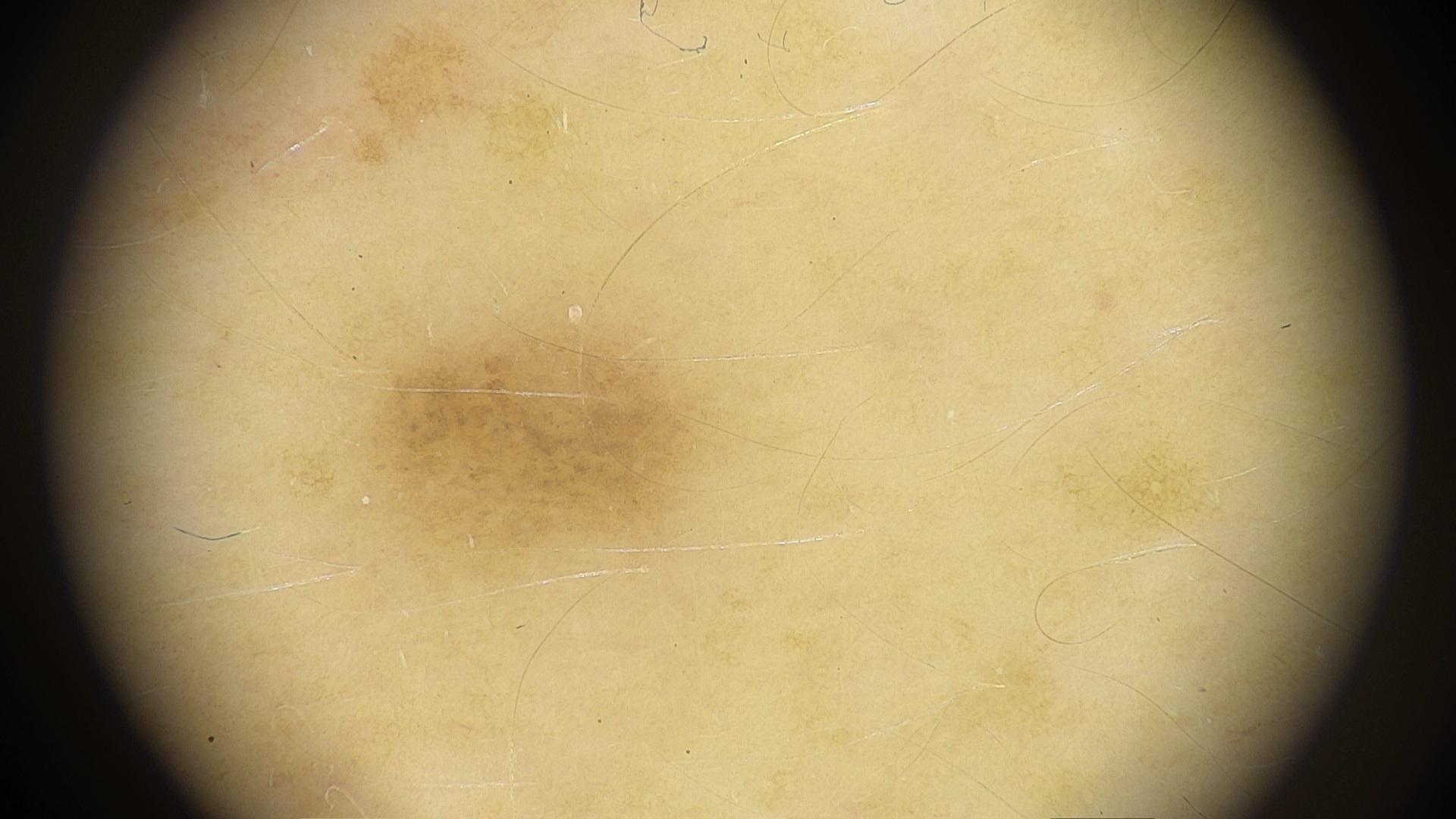body site = the posterior trunk; impression = Nevus.